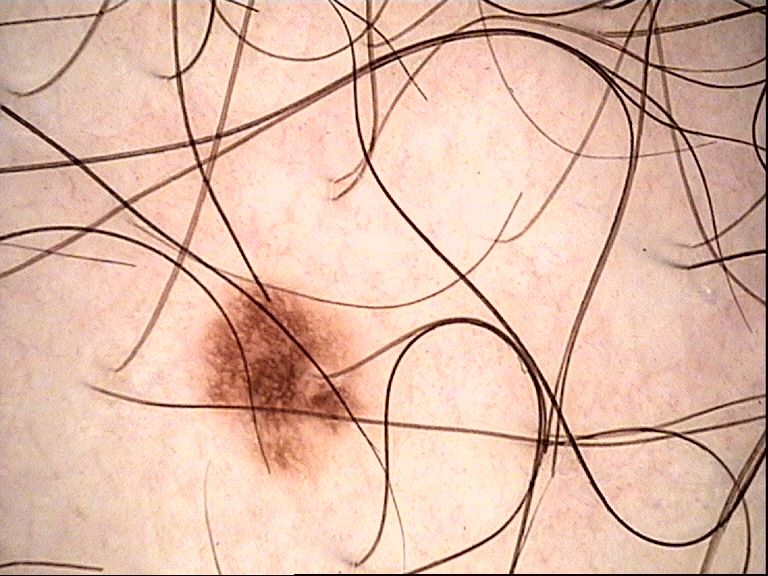Case: A dermatoscopic image of a skin lesion. Impression: The diagnosis was a dysplastic junctional nevus.